The patient is skin type II. By history, pesticide exposure. A clinical close-up photograph of a skin lesion. A male patient 46 years old:
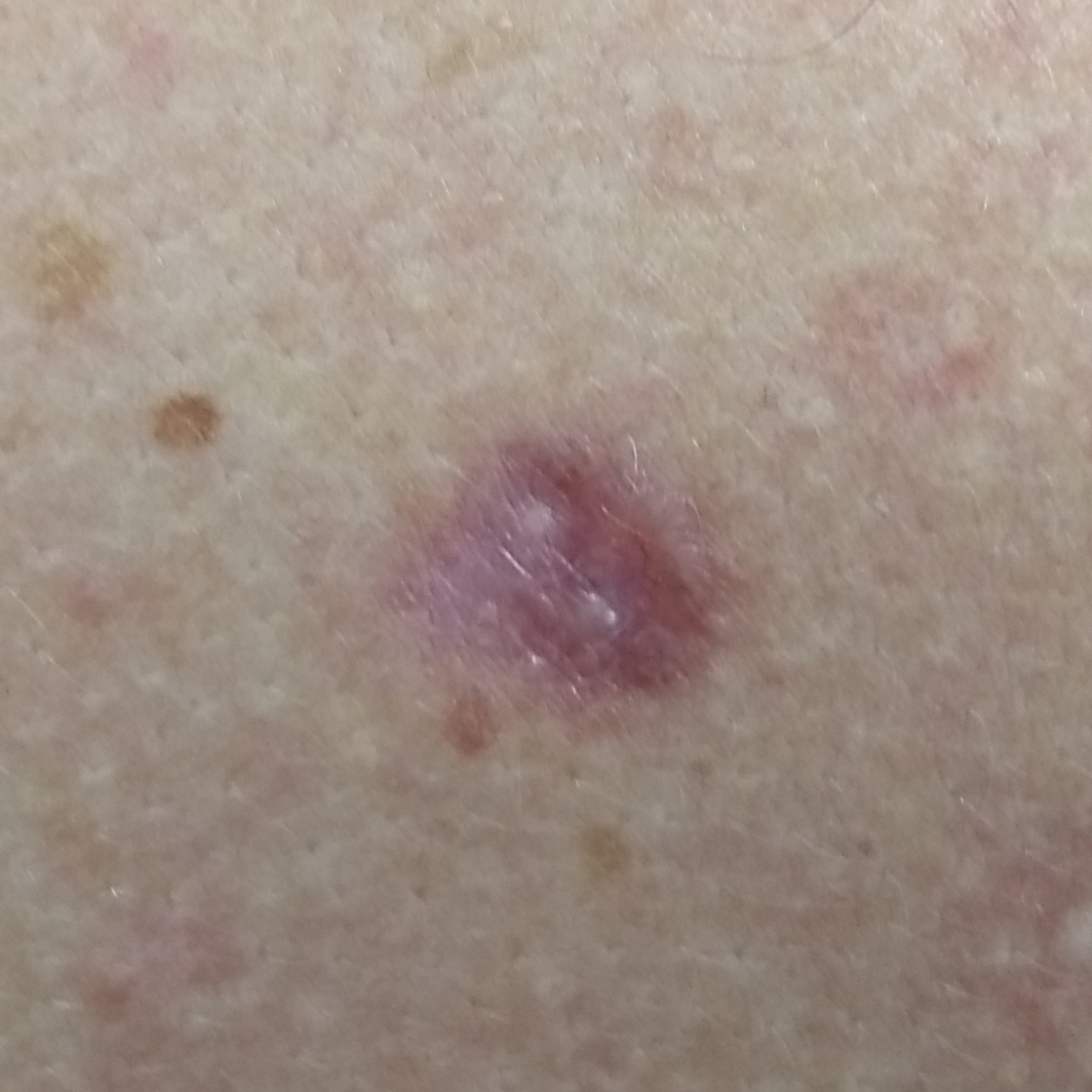Findings:
– location · the chest
– lesion diameter · 4 × 4 mm
– patient-reported symptoms · elevation
– pathology · basal cell carcinoma (biopsy-proven)